A dermatoscopic image of a skin lesion:
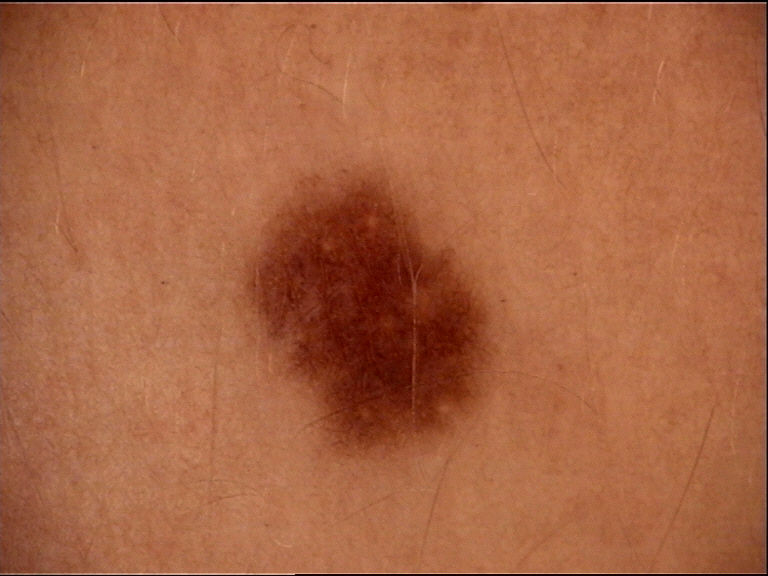The diagnosis was a dysplastic junctional nevus.